A female subject aged 33 to 37; contact-polarized dermoscopy of a skin lesion; recorded as Fitzpatrick skin type II: 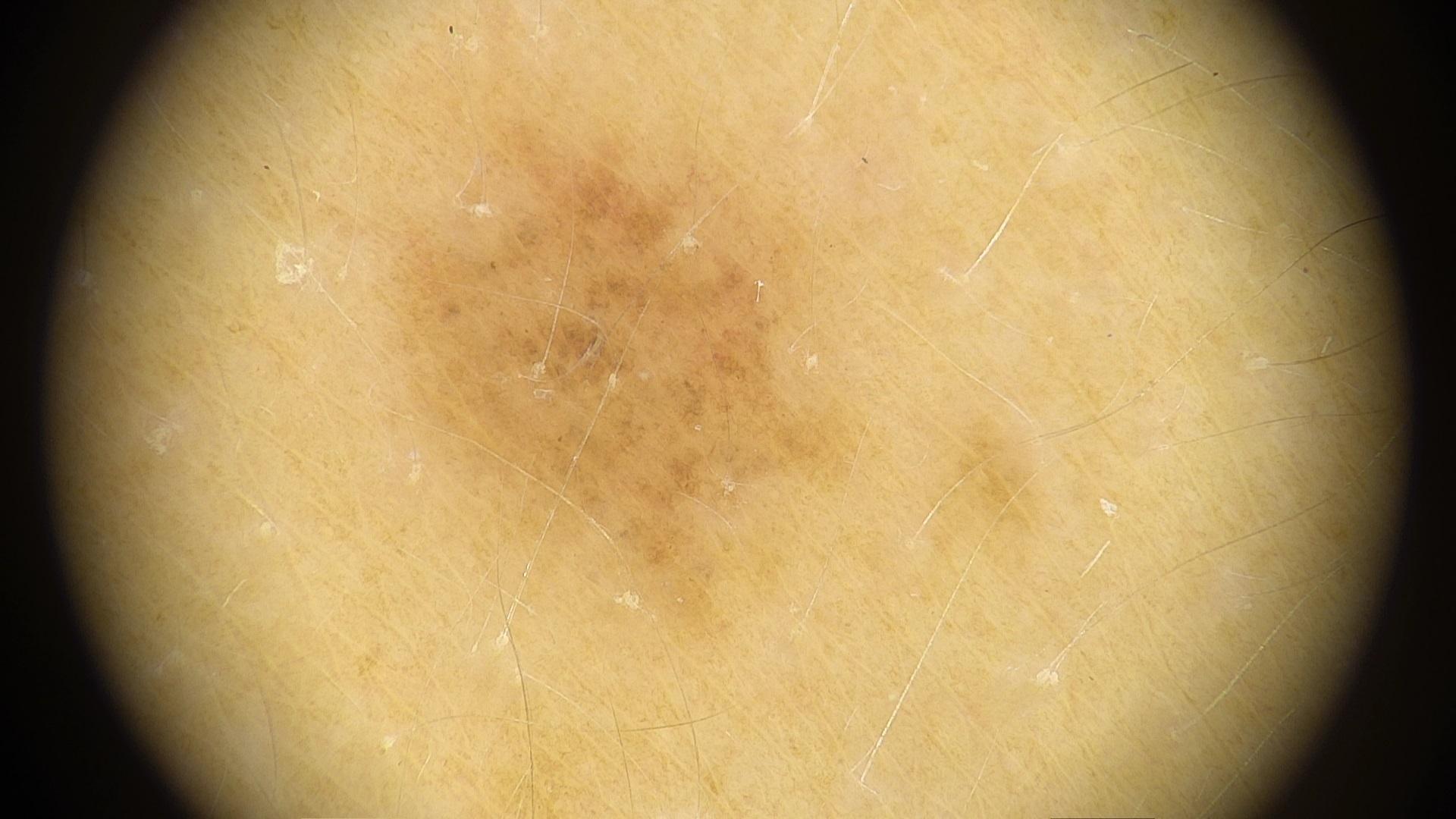Clinically diagnosed as a benign, melanocytic lesion — a nevus.